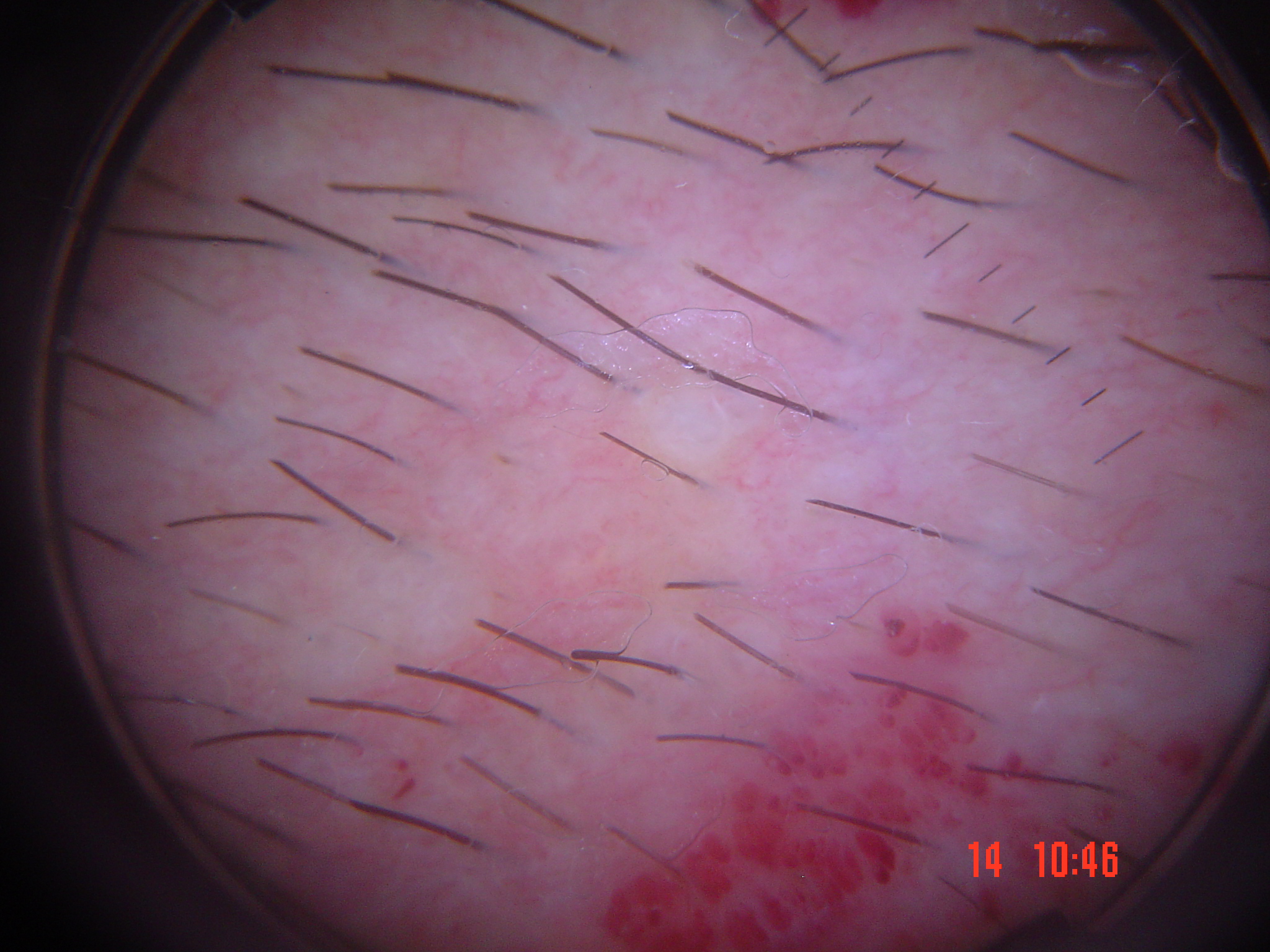lesion type = vascular; label = lymphangioma (expert consensus).